Symptoms reported: bothersome appearance and enlargement; texture is reported as flat; self-categorized by the patient as a rash; the photograph was taken at a distance; the condition has been present for one to four weeks; the patient also reports joint pain, chills and fatigue; located on the back of the torso, front of the torso, leg and arm:
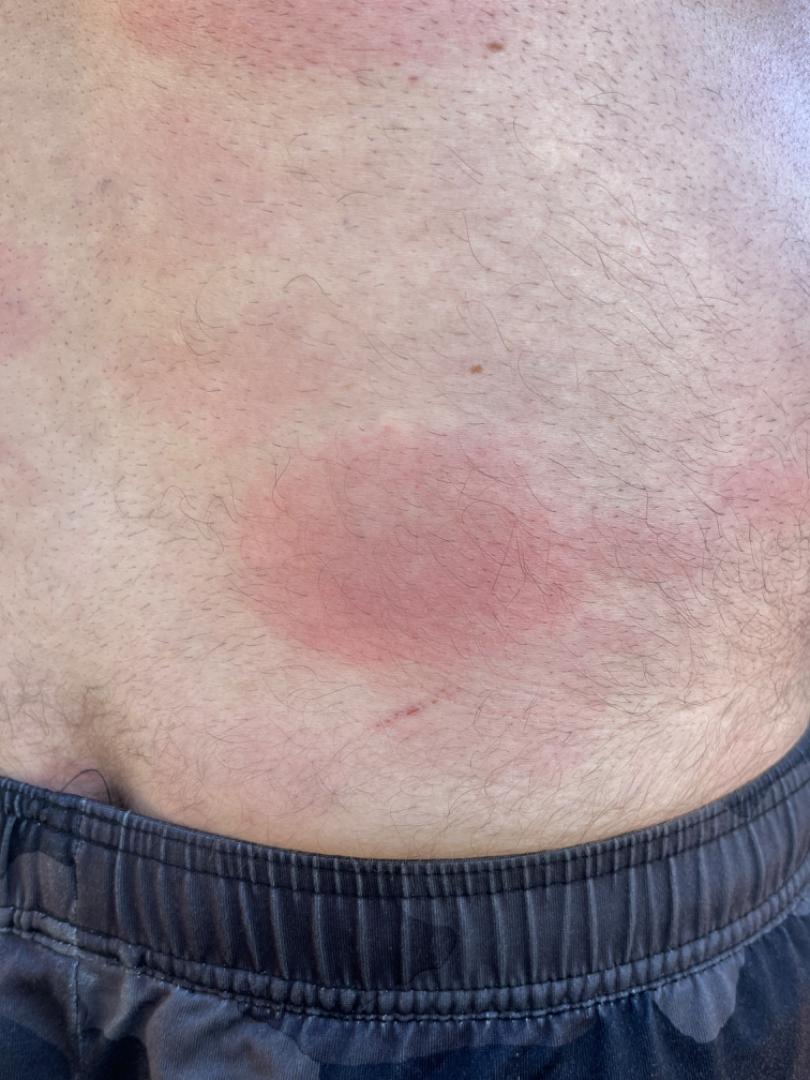<dermatology_case>
  <assessment>unable to determine</assessment>
</dermatology_case>